Dermoscopy of a skin lesion.
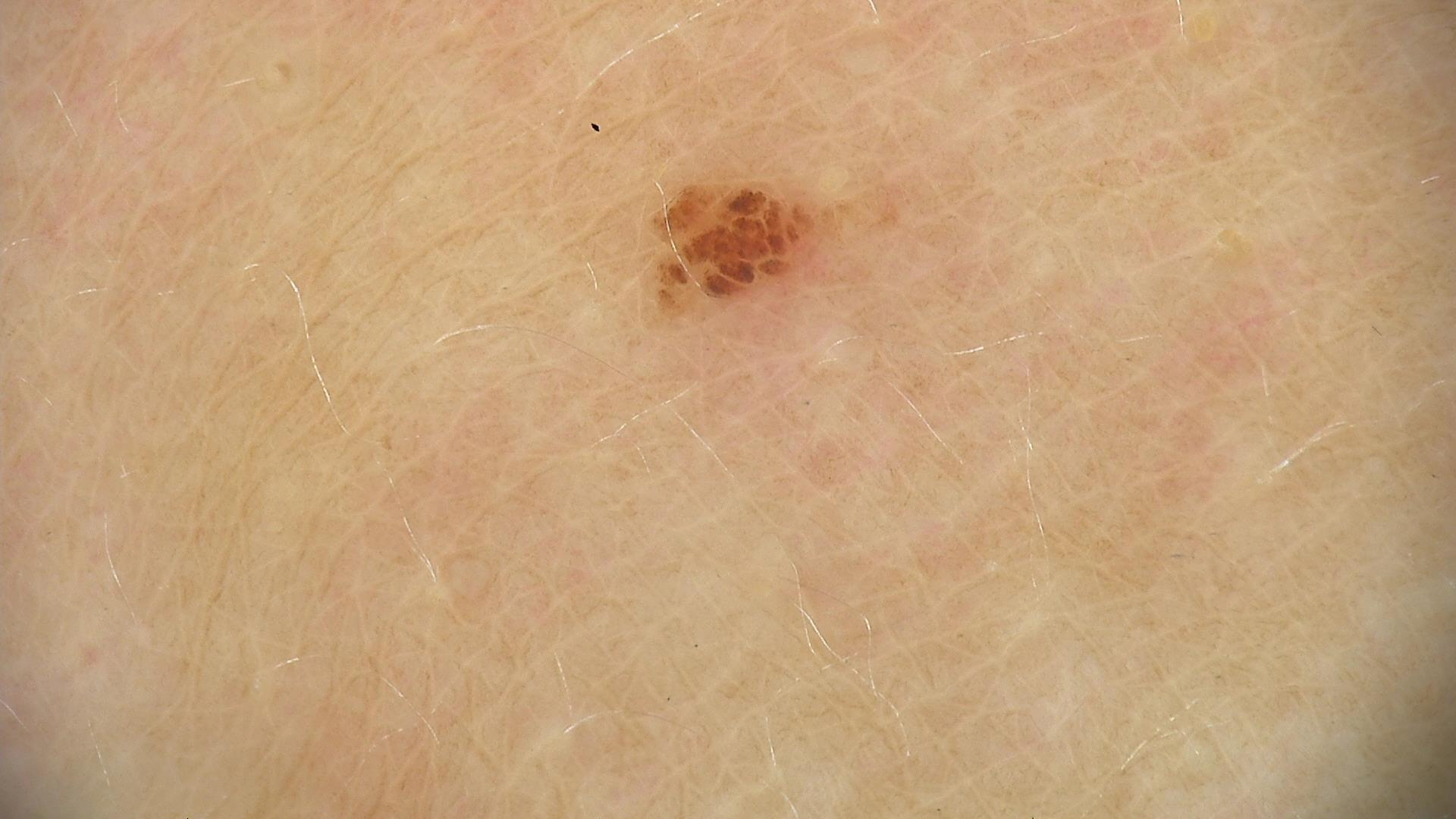diagnosis=dysplastic junctional nevus (expert consensus).